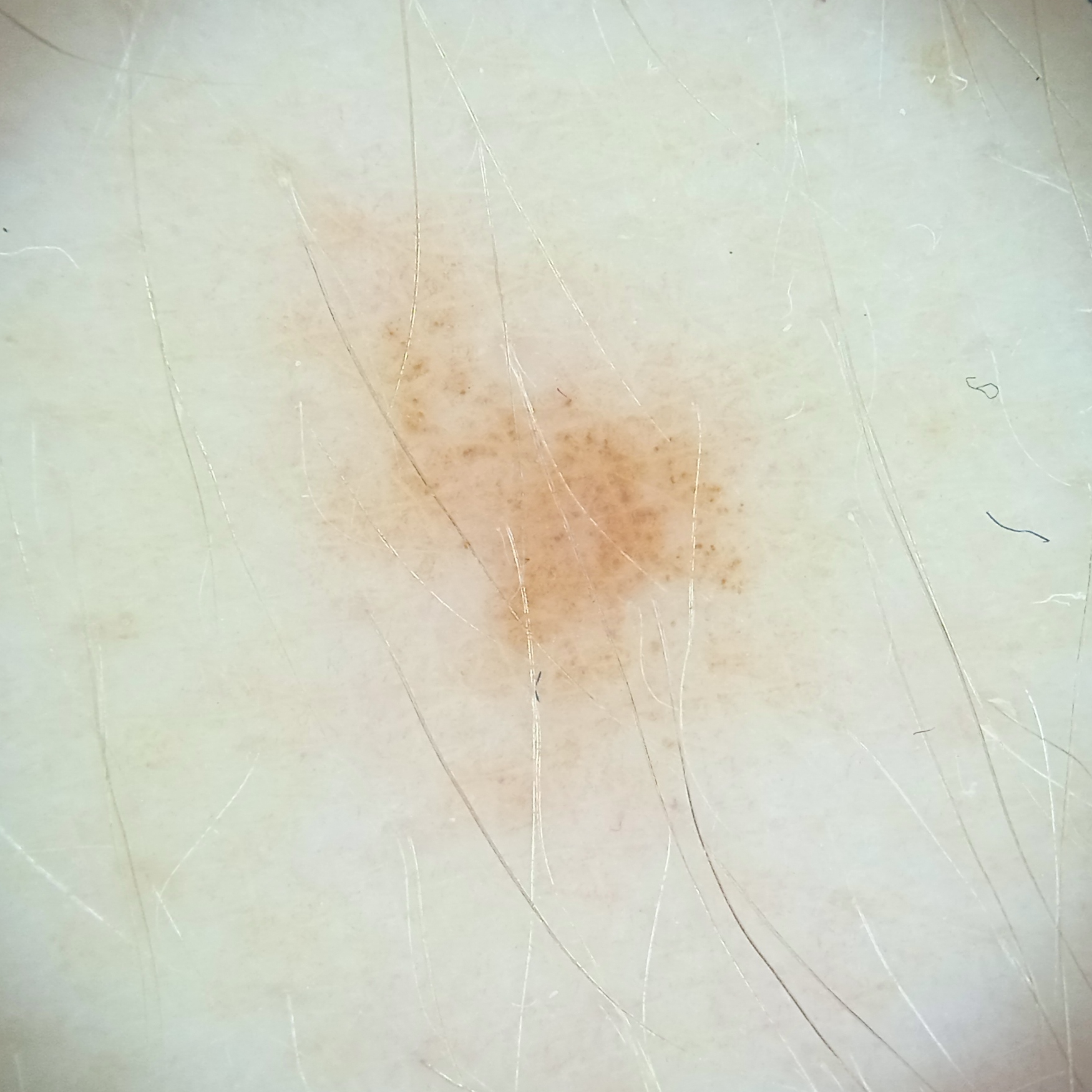Collected as part of a research study, without a referral diagnosis.
A female subject 39 years of age.
The patient says their skin reddens with sun exposure.
The patient describes having few moles overall.
A skin lesion imaged with a dermatoscope.
The dermatologists' assessment was a melanocytic nevus.